Texture is reported as raised or bumpy. Reported duration is about one day. Located on the arm. The photograph was taken at a distance. The patient described the issue as a rash. Female patient, age 18–29. Reported lesion symptoms include itching and bothersome appearance. No associated systemic symptoms reported: 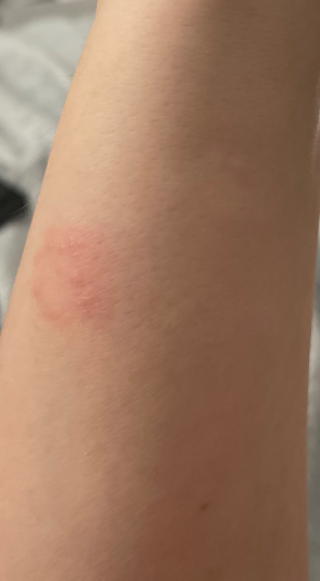<dermatology_case>
  <assessment>no skin condition identified</assessment>
</dermatology_case>